A dermatoscopic image of a skin lesion · a male subject, aged around 75: 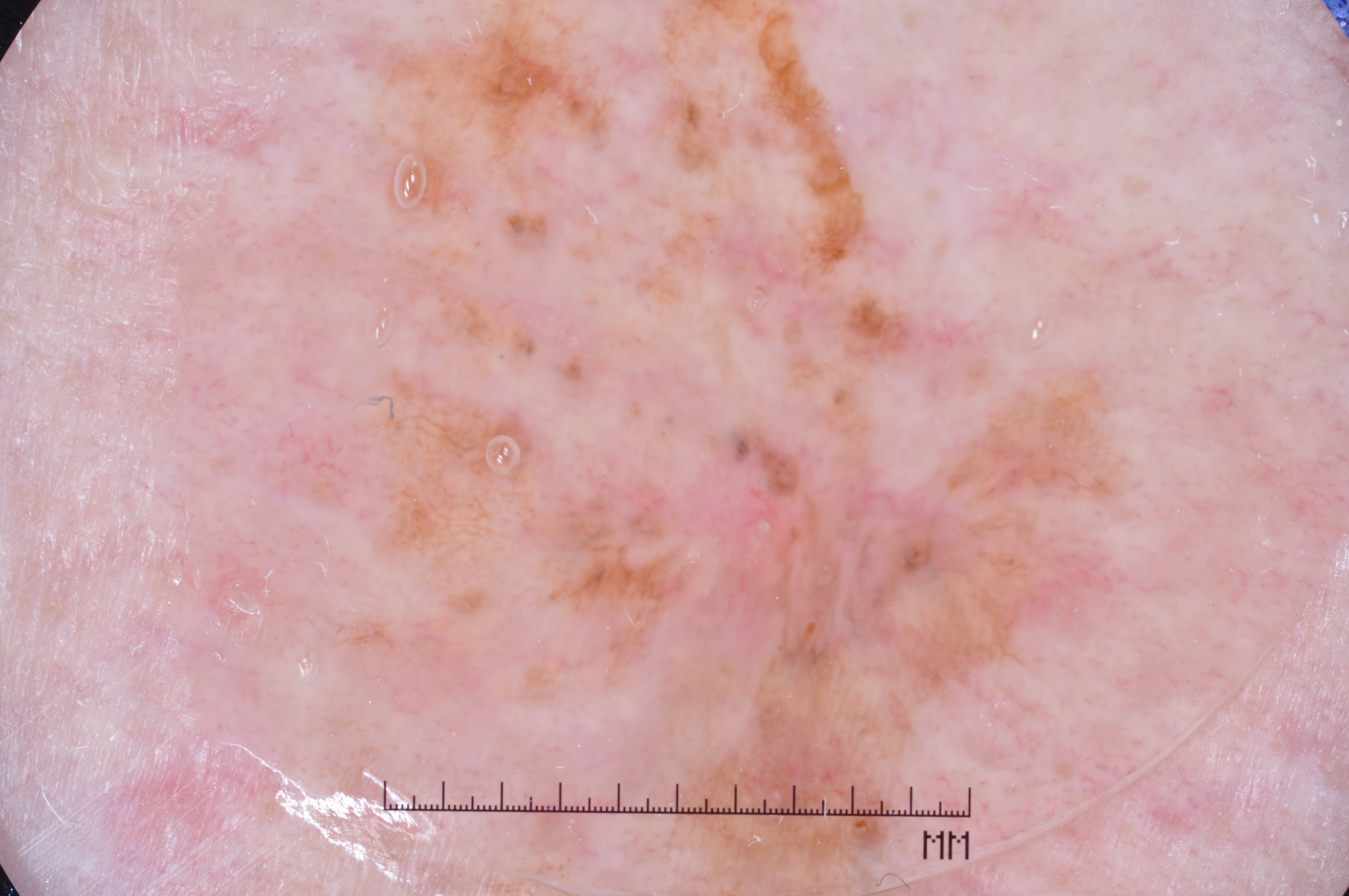Dermoscopic assessment notes pigment network. The visible lesion spans x1=282, y1=2, x2=1162, y2=894. A prominent lesion filling much of the field. Histopathologically confirmed as a melanoma.